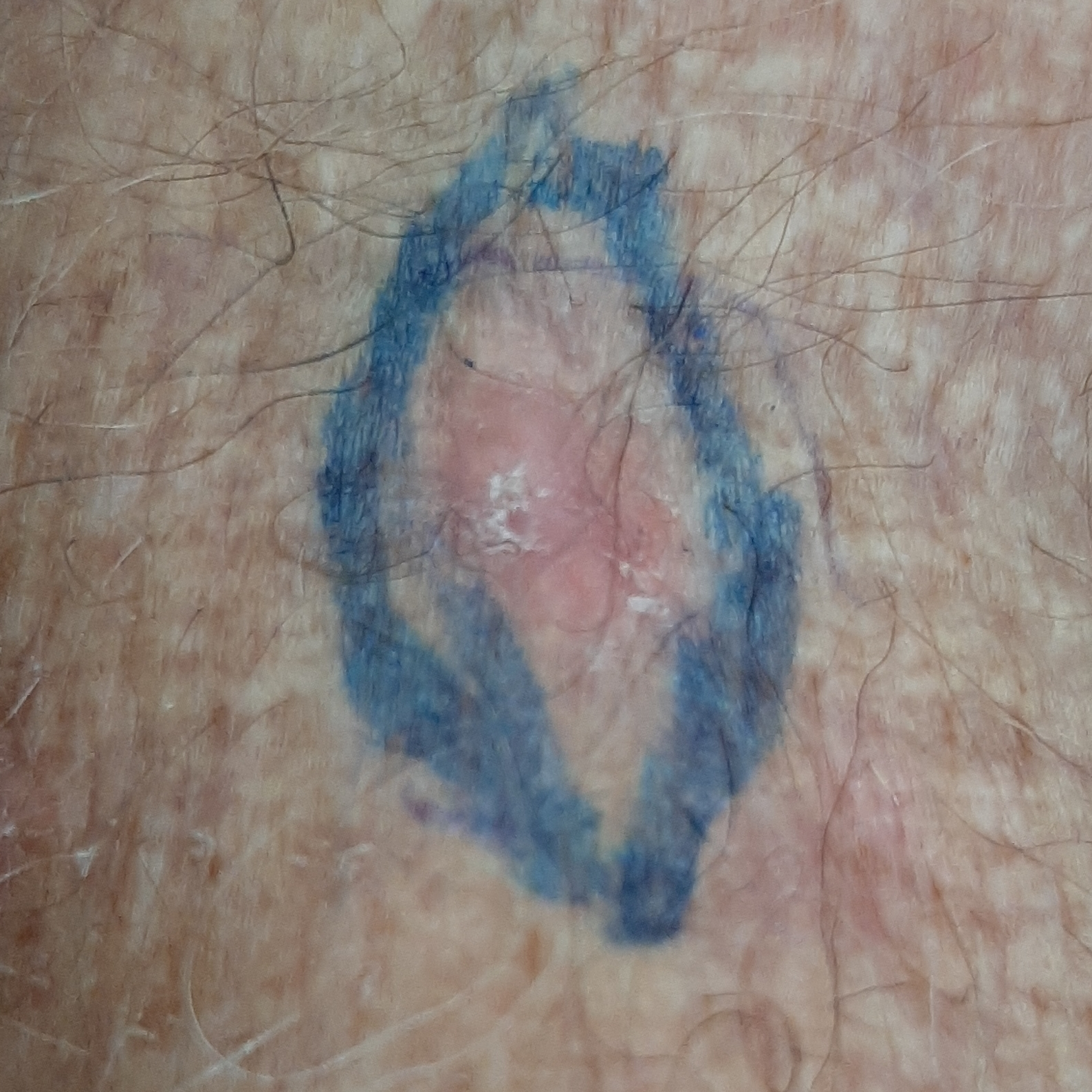  patient:
    age: 70
    gender: male
  skin_type: II
  image: clinical photo
  lesion_location: a forearm
  lesion_size:
    diameter_1_mm: 10.0
    diameter_2_mm: 8.0
  symptoms:
    present:
      - itching
  diagnosis:
    name: actinic keratosis
    code: ACK
    malignancy: indeterminate
    confirmation: histopathology